The patient says their skin tans without first burning; a female patient 78 years old; collected as part of a research study, without a referral diagnosis; numerous moles by the patient's own estimate; dermoscopy of a skin lesion — 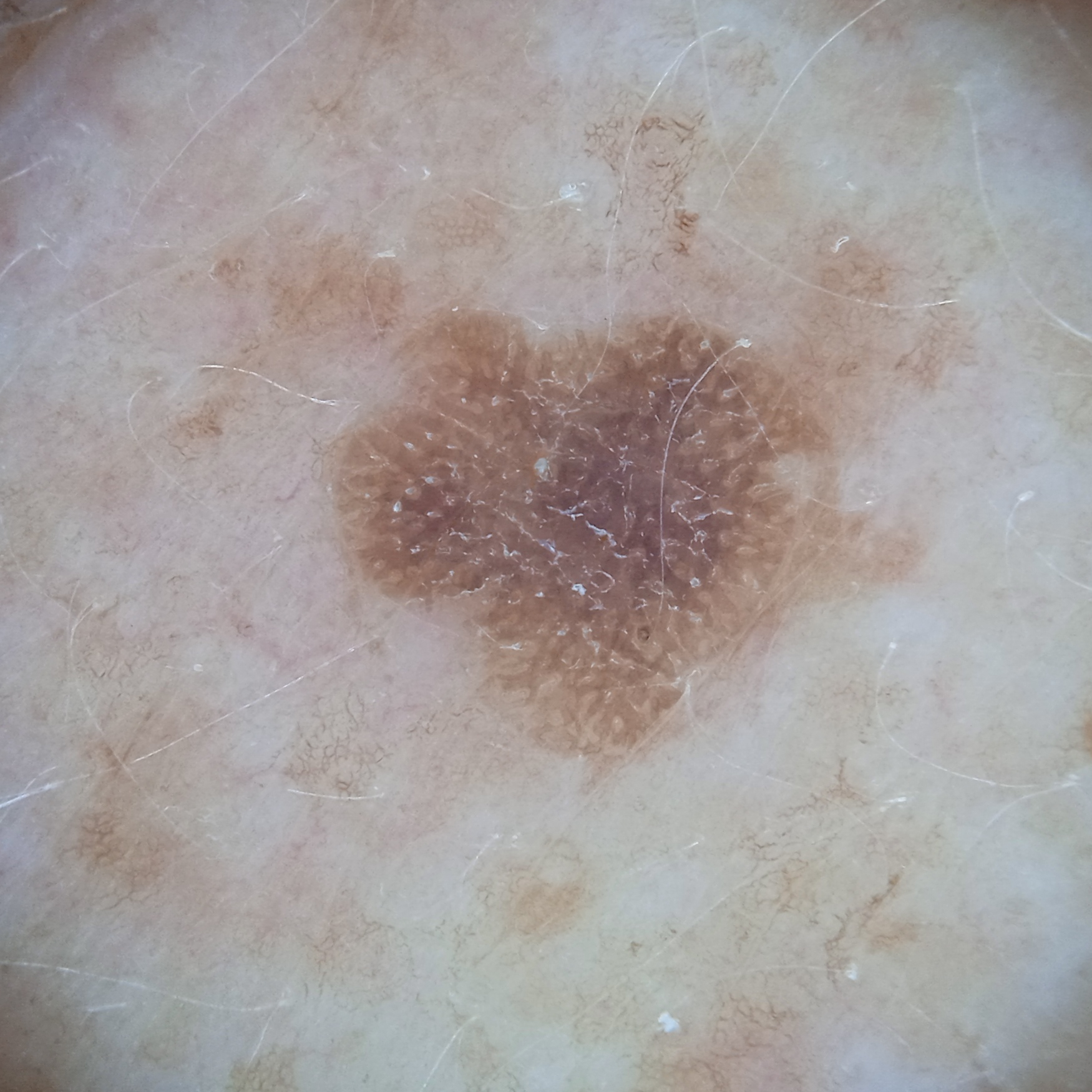Q: Where is the lesion?
A: the back
Q: Lesion size?
A: 5.6 mm
Q: What was the diagnosis?
A: seborrheic keratosis (dermatologist consensus)